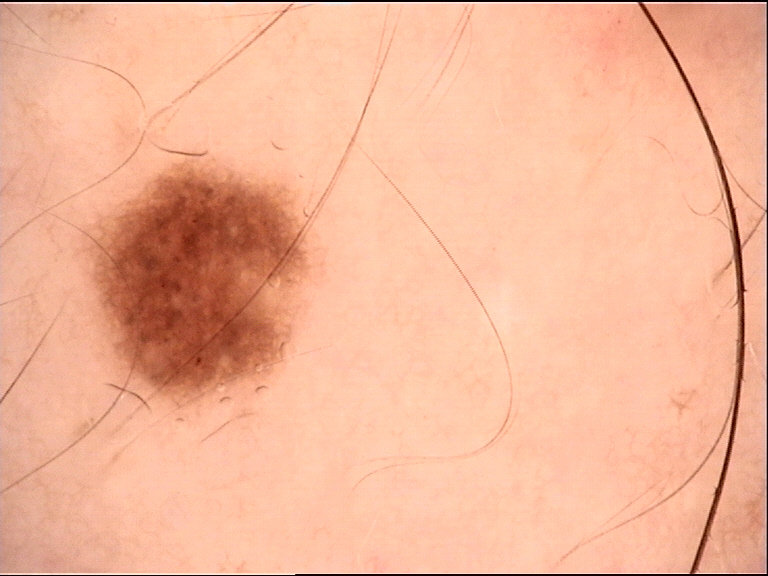Case:
- image type · dermoscopy
- diagnosis · dysplastic junctional nevus (expert consensus)